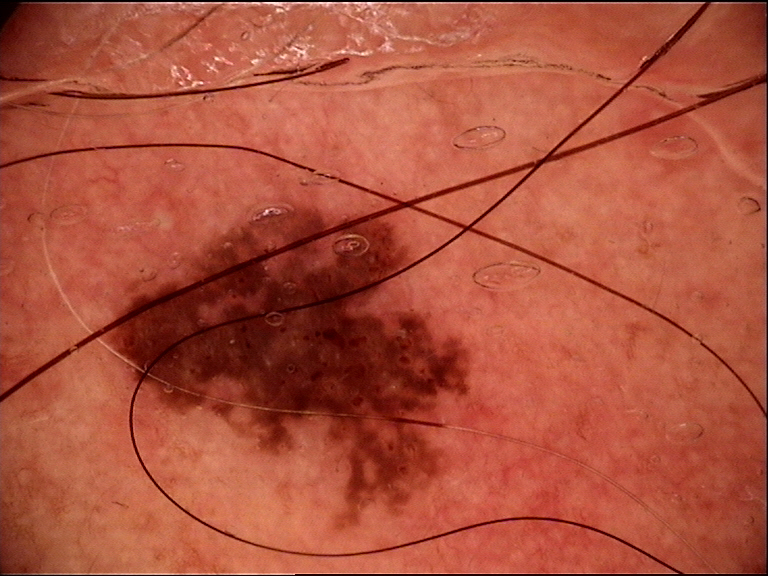class: lentigo maligna (biopsy-proven).